Located on the palm and arm, the photograph is a close-up of the affected area.
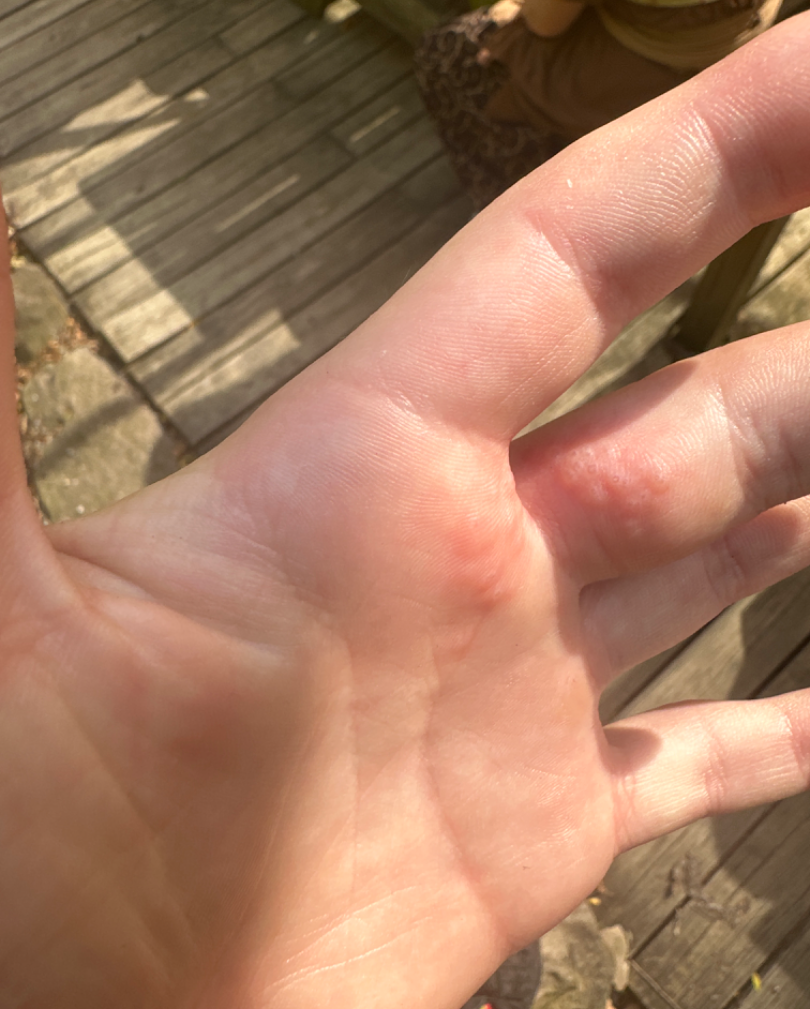FST I. Texture is reported as raised or bumpy. The lesion is associated with pain, itching and burning. Favoring Herpes Simplex.